A dermoscopy image of a single skin lesion:
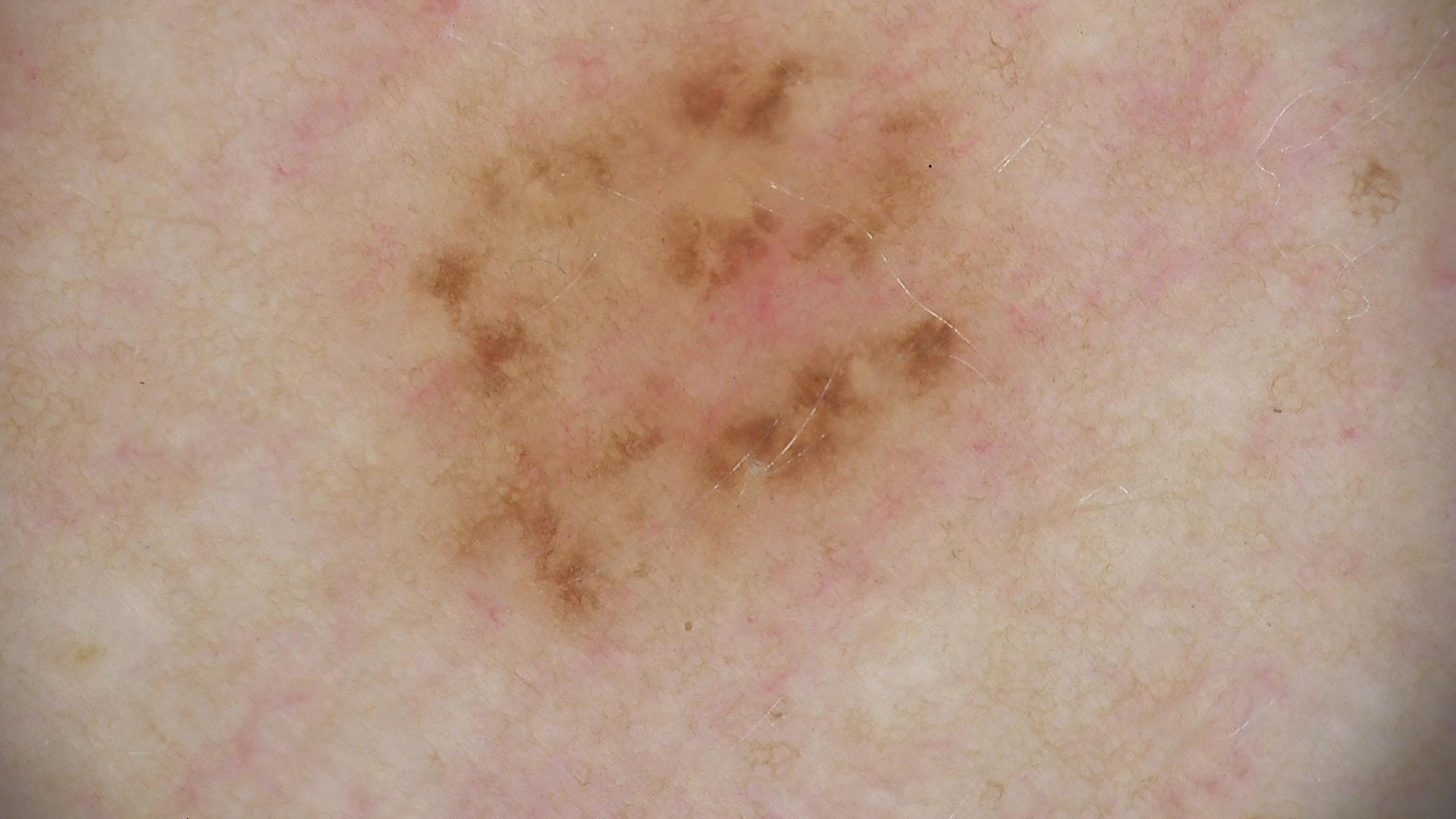Impression:
Classified as a dysplastic junctional nevus.